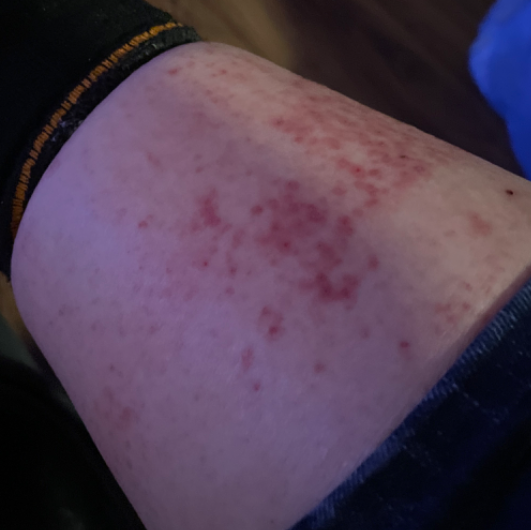The reviewing panel's impression was: Eczema (most likely); Irritant Contact Dermatitis (possible); Folliculitis (unlikely); Xerosis (unlikely); Stasis Dermatitis (unlikely); Leukocytoclastic Vasculitis (unlikely).